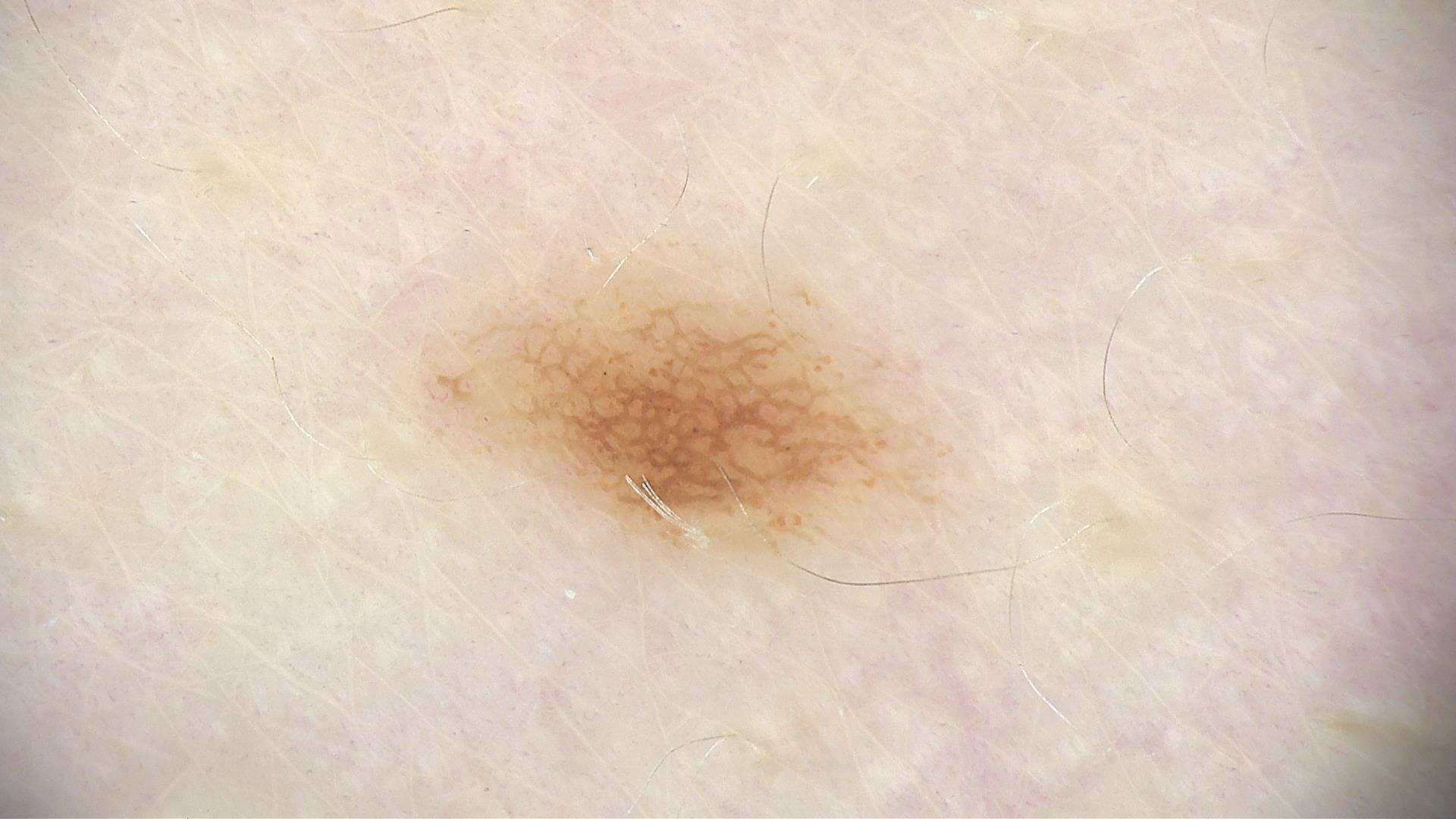Conclusion: The diagnostic label was a dysplastic junctional nevus.